A dermoscopy image of a single skin lesion.
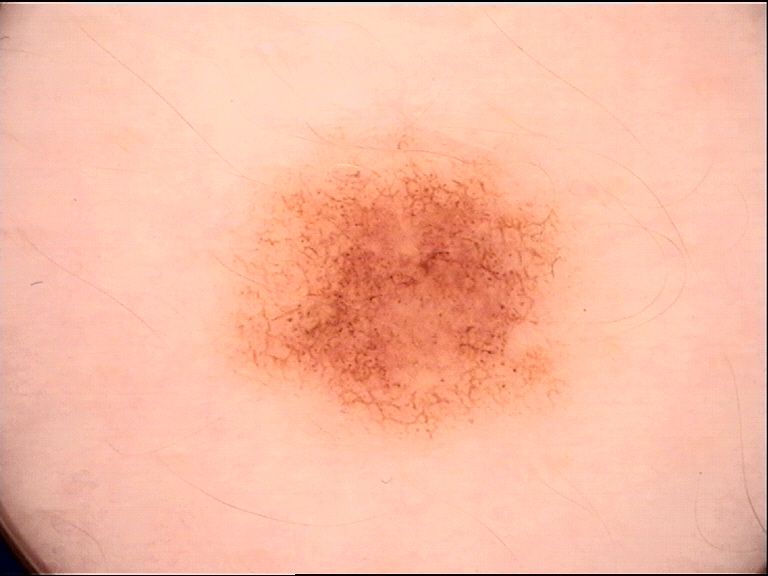diagnostic label=dysplastic junctional nevus (expert consensus).